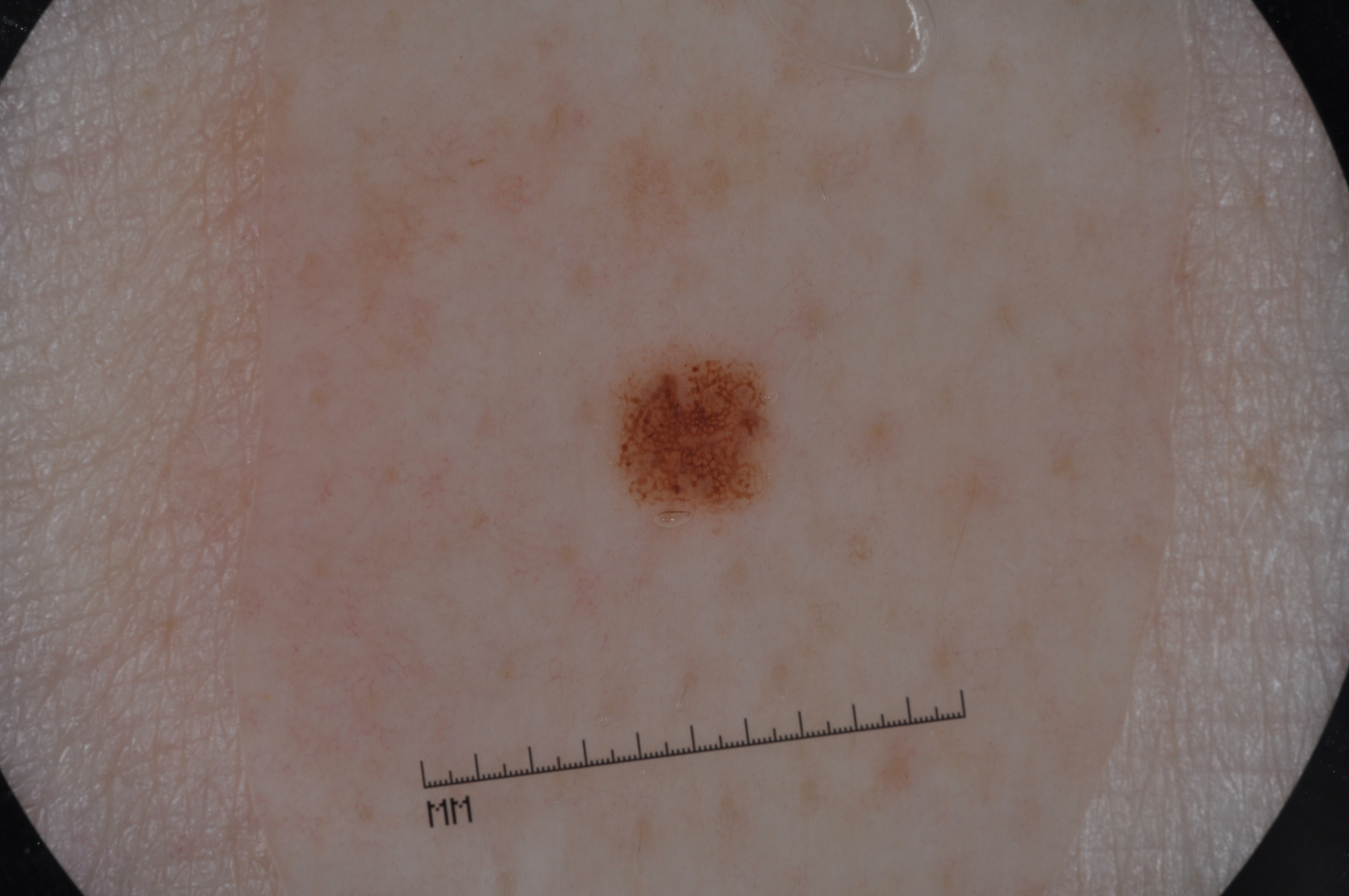imaging — dermoscopic image | patient — female, roughly 50 years of age | lesion bbox — left=611, top=357, right=769, bottom=511 | dermoscopic features — pigment network; absent: streaks, milia-like cysts, and negative network | extent — ~2% of the field | assessment — a melanocytic nevus, a benign skin lesion.